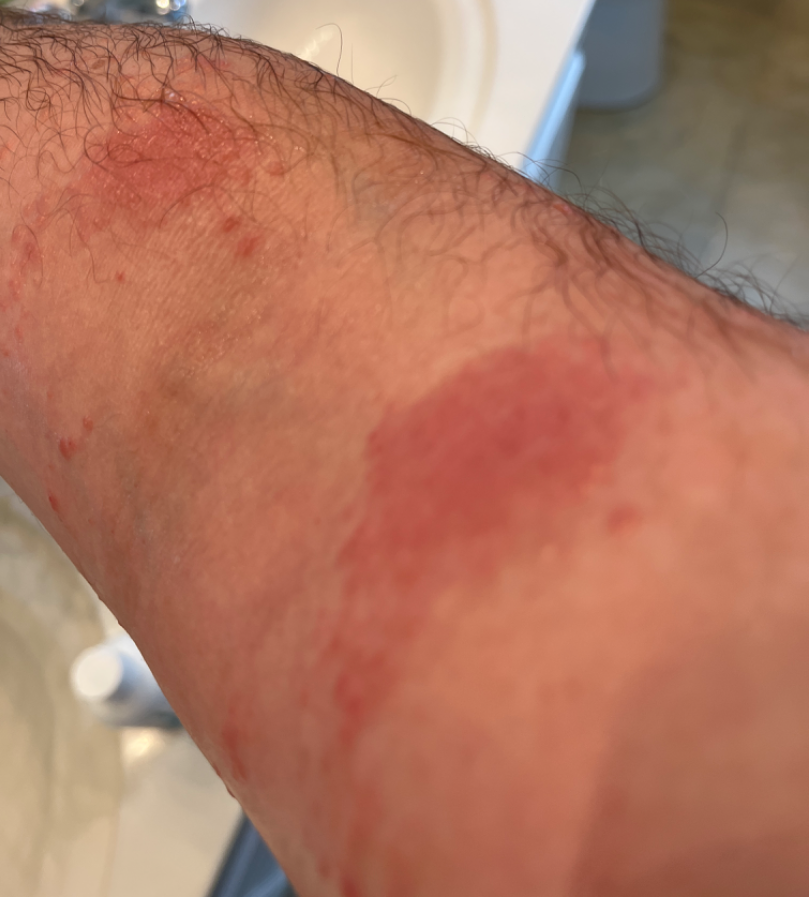assessment: ungradable on photographic review; described texture: fluid-filled, rough or flaky and raised or bumpy; shot type: close-up; onset: less than one week; contributor: male, age 30–39; anatomic site: head or neck, leg and arm.